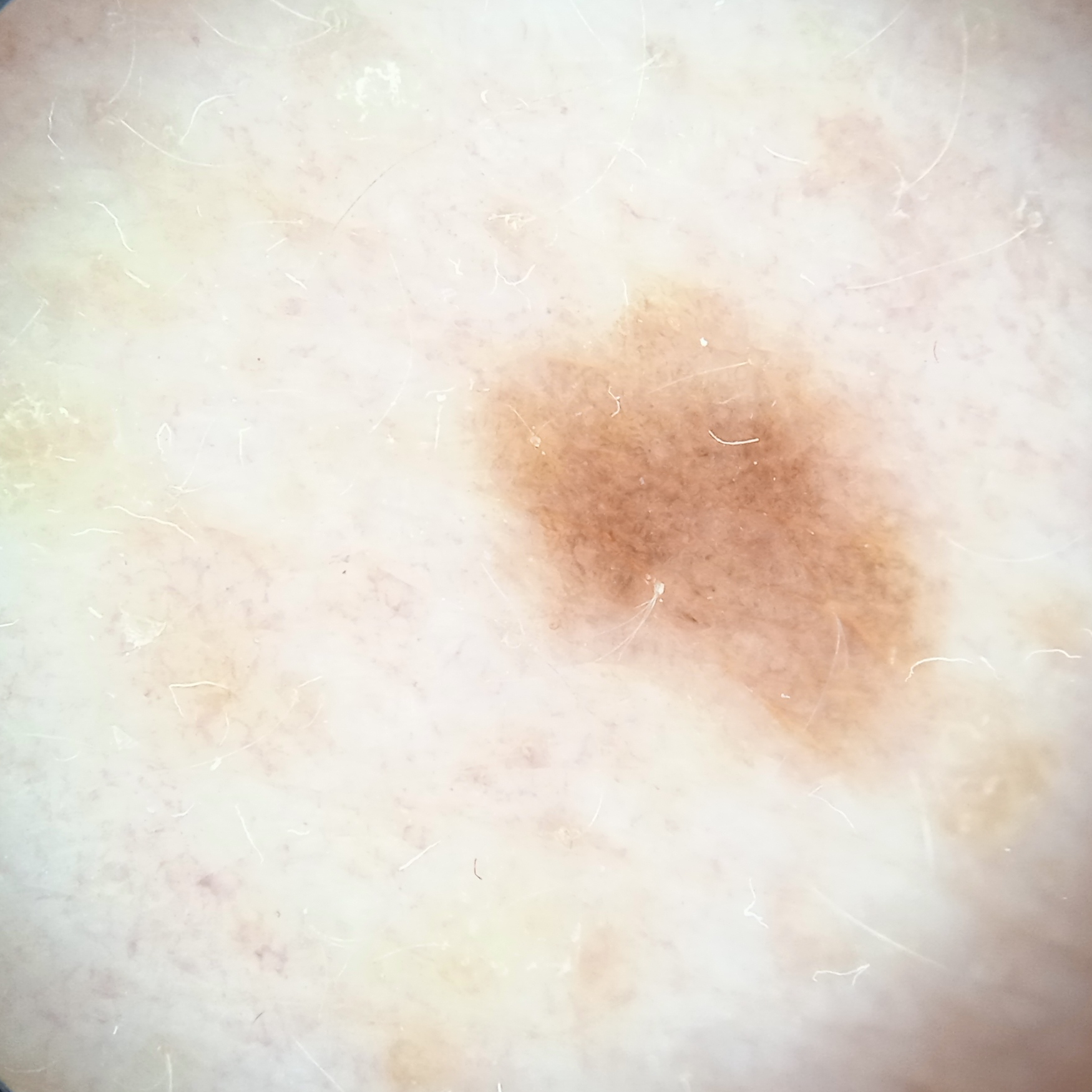On a questionnaire the patient reported immunosuppression and a prior organ transplant. Collected as part of a research study, without a referral diagnosis. The patient describes having a moderate number of moles. The patient says their skin reddens painfully with sun exposure. A female patient aged 55. The lesion measures approximately 6.3 mm. The dermatologists' assessment was a melanocytic nevus.